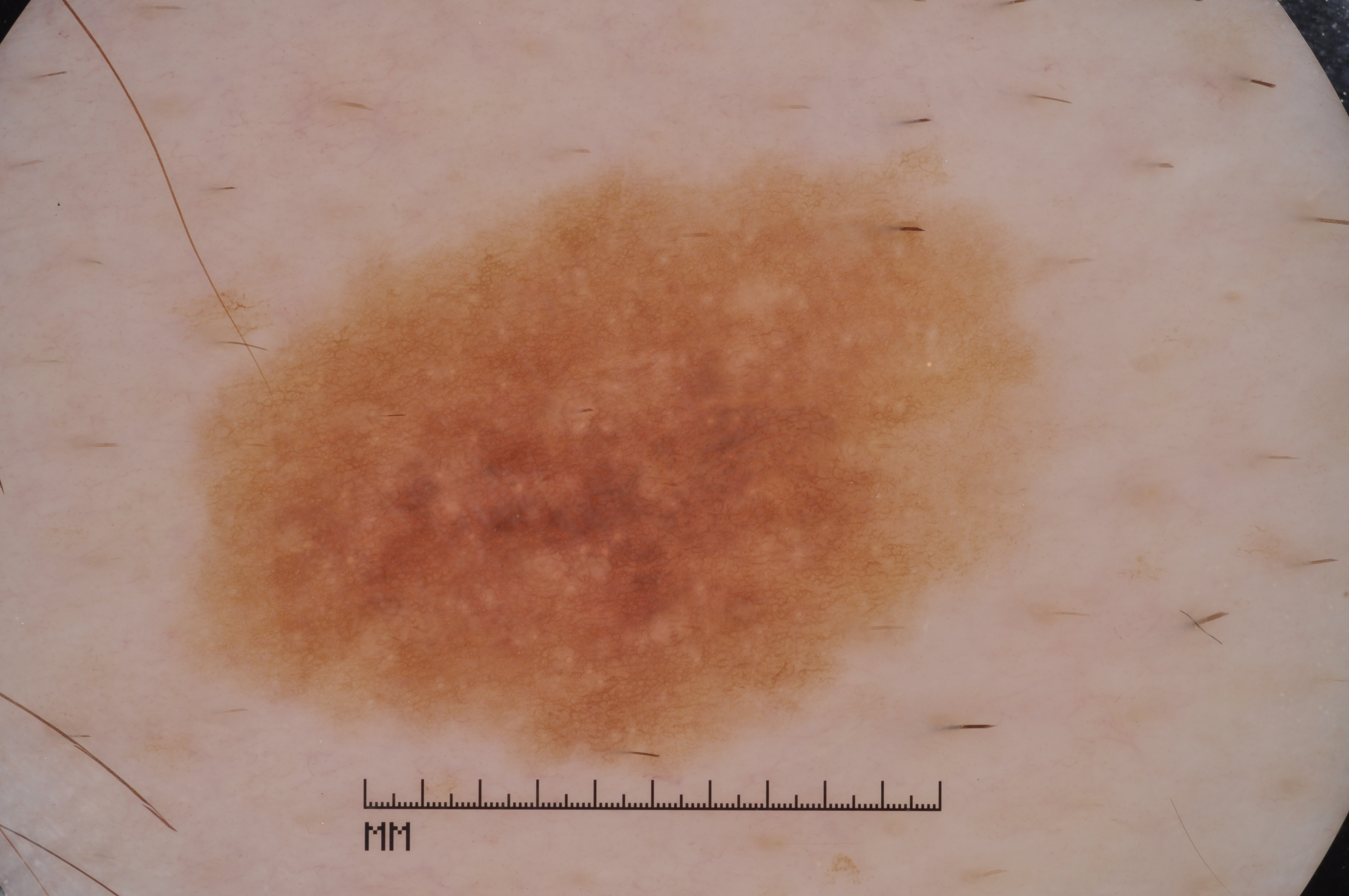A male subject approximately 60 years of age.
A dermoscopy image of a single skin lesion.
A prominent lesion filling much of the field.
With coordinates (x1, y1, x2, y2), the lesion occupies the region 201, 161, 1043, 763.
Dermoscopy demonstrates pigment network.
On biopsy, the diagnosis was a melanoma, a malignant lesion.